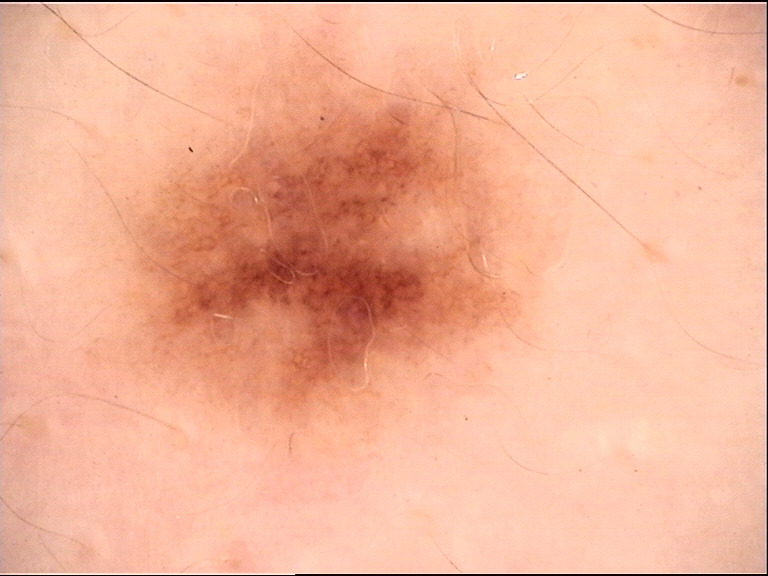<dermoscopy>
<diagnosis>
<name>dysplastic junctional nevus</name>
<code>jd</code>
<malignancy>benign</malignancy>
<super_class>melanocytic</super_class>
<confirmation>expert consensus</confirmation>
</diagnosis>
</dermoscopy>